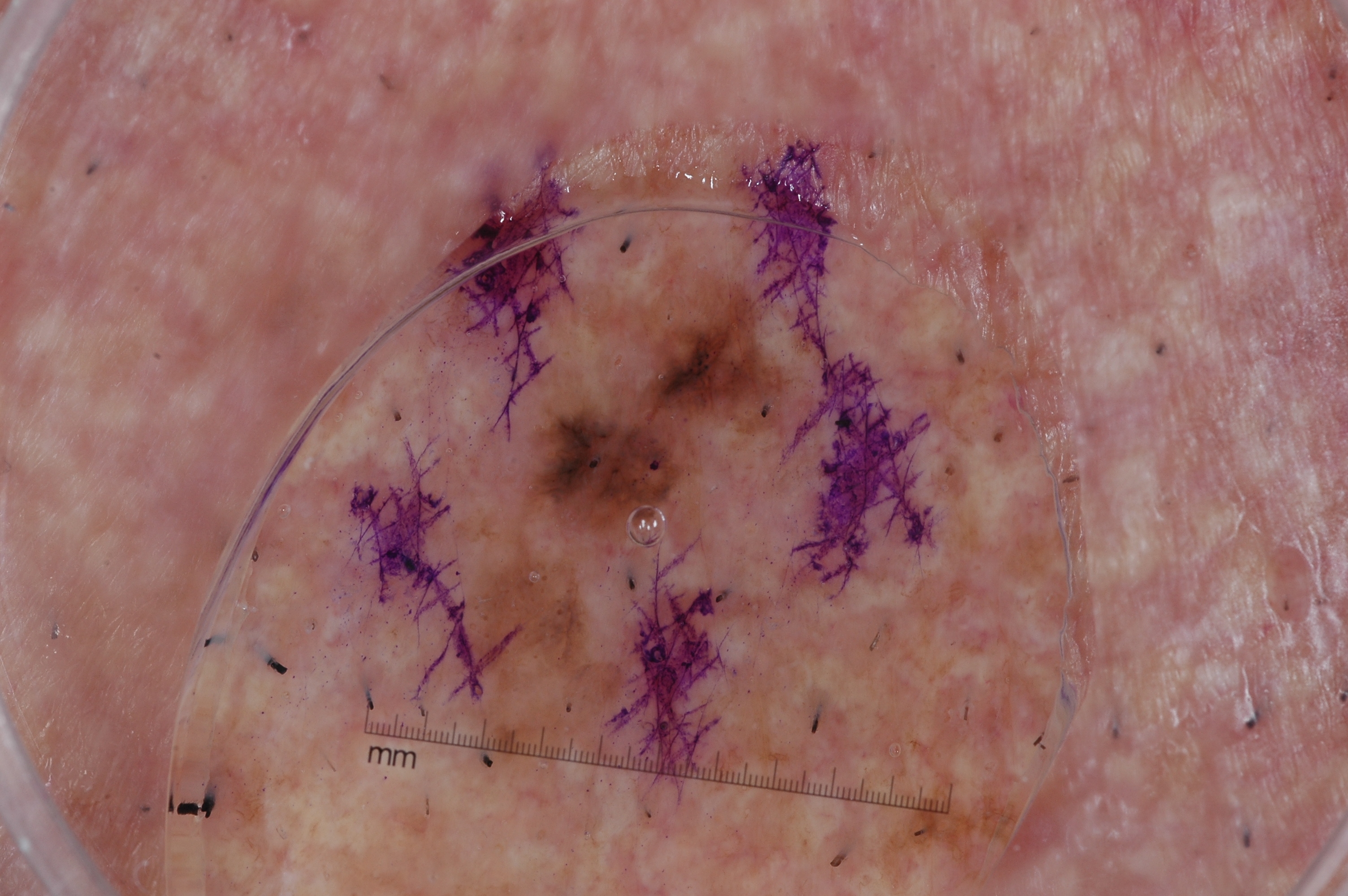Q: What kind of image is this?
A: dermatoscopic image of a skin lesion
Q: Who is the patient?
A: male, roughly 80 years of age
Q: What does dermoscopy show?
A: pigment network
Q: What is the lesion's bounding box?
A: 332 234 815 824
Q: How large is the lesion within the image?
A: ~16% of the field
Q: What is this lesion?
A: a melanoma